A skin lesion imaged with a dermatoscope.
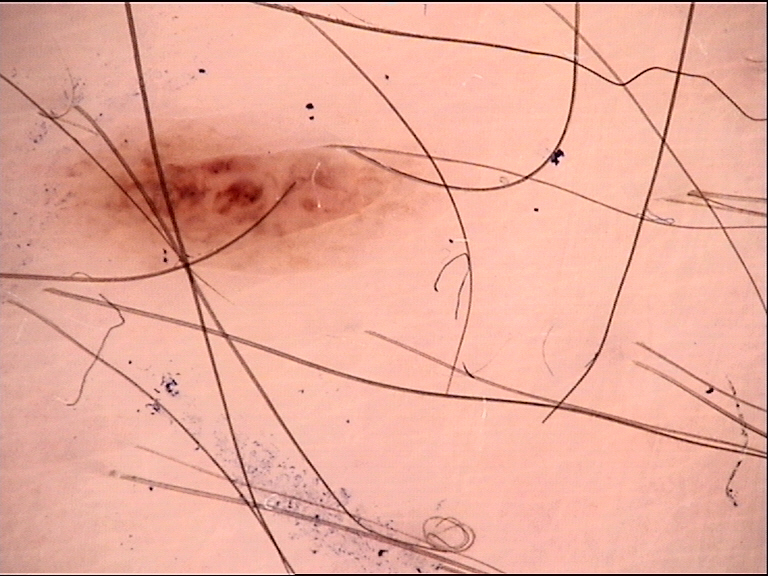subtype: banal
diagnosis: compound nevus (expert consensus)